Dermoscopy of a skin lesion:
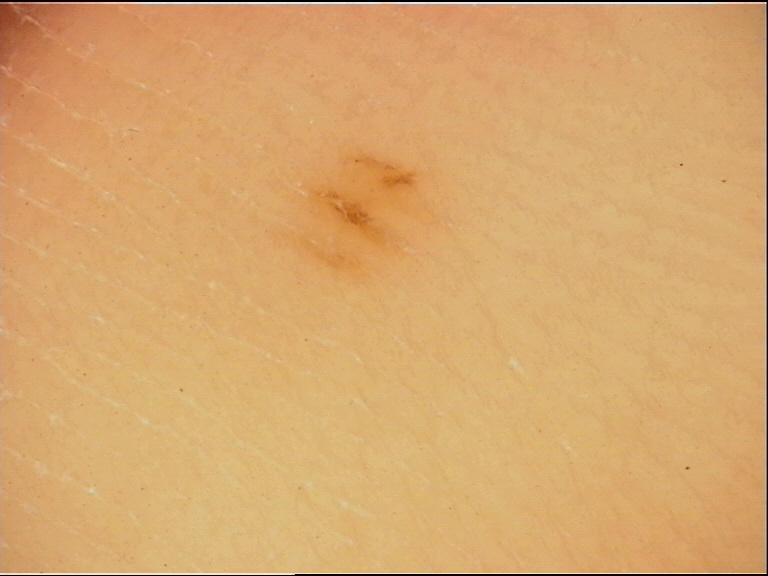Consistent with an acral junctional nevus.